The photograph was taken at an angle. Self-categorized by the patient as a rash. The lesion involves the head or neck. The patient reports the lesion is fluid-filled. The subject is male — 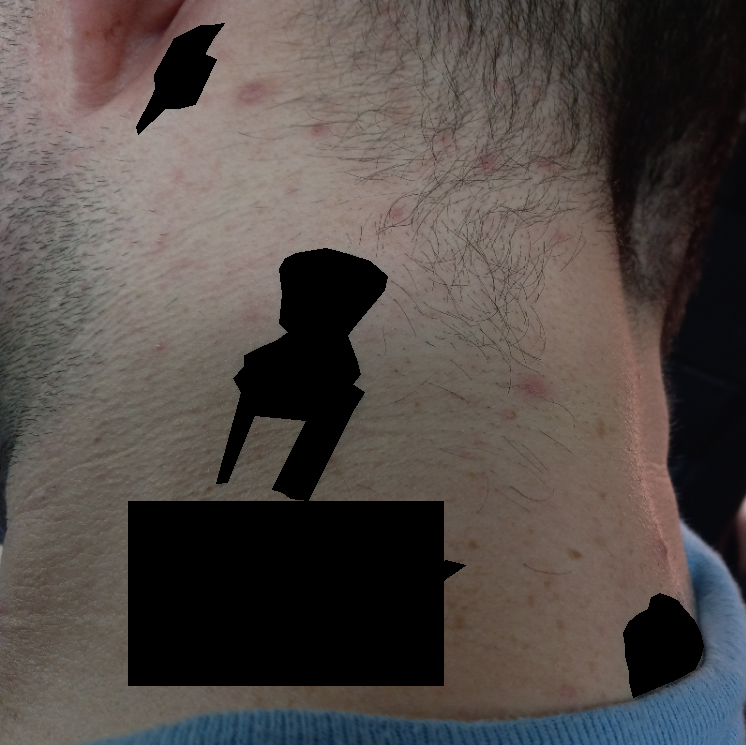On remote dermatologist review: the favored diagnosis is Acne.